Texture is reported as raised or bumpy; the subject is 30–39, female; the patient notes itching, enlargement and burning; close-up view; located on the front of the torso; the patient considered this a rash; Fitzpatrick phototype II:
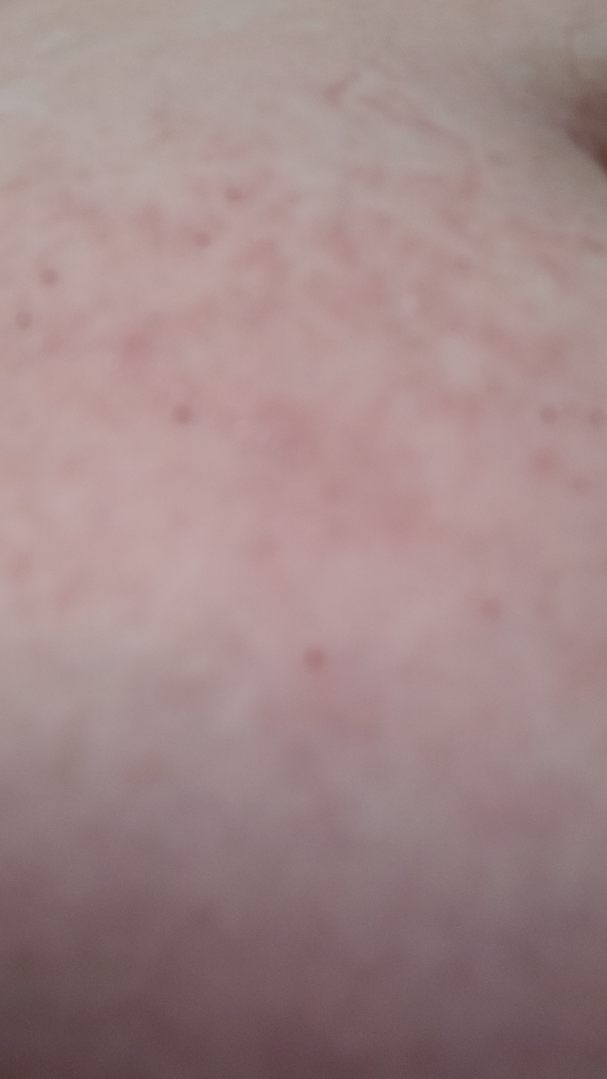Review: The case was difficult to assess from the available photograph.